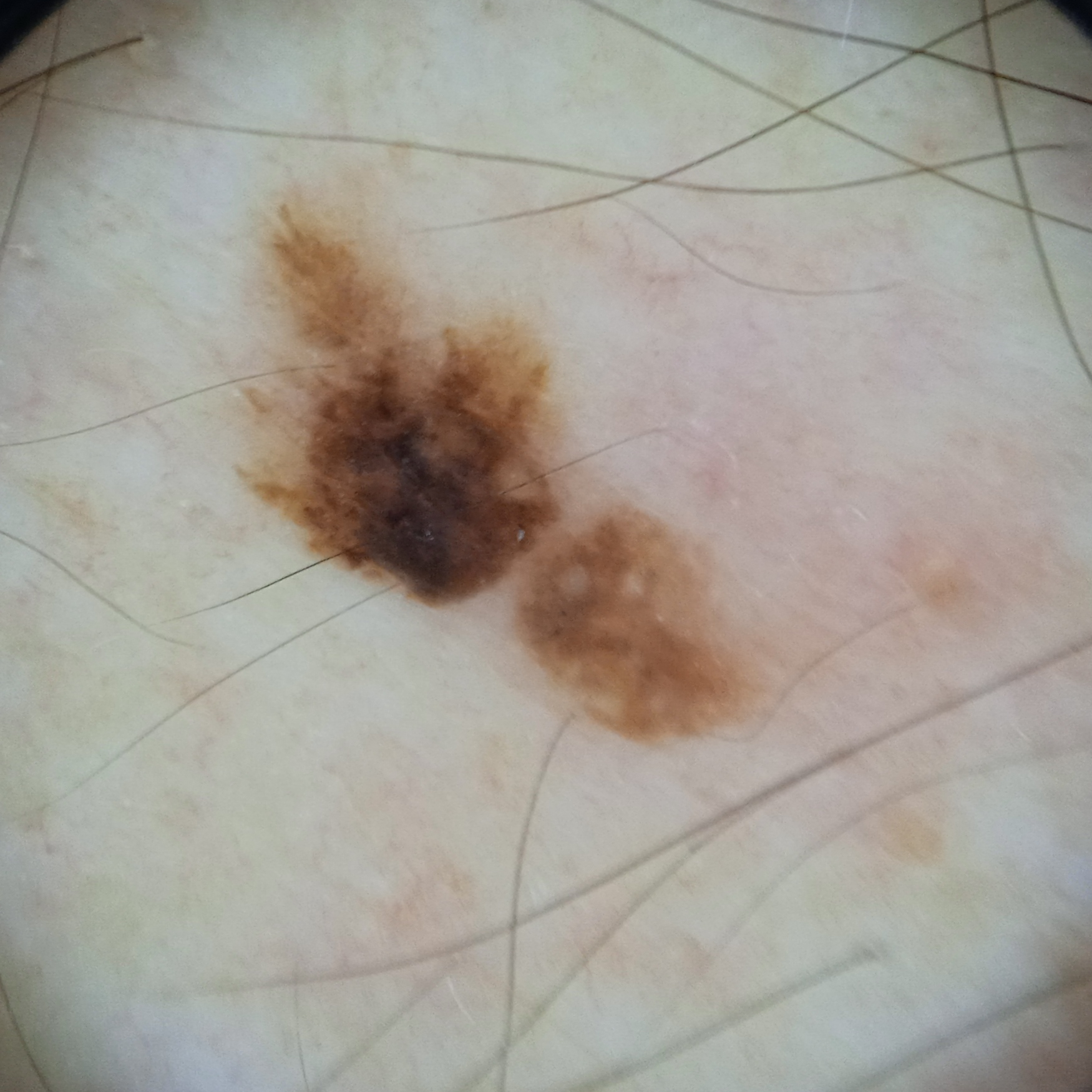{
  "image": "dermoscopy",
  "referral": "research study (no referral diagnosis)",
  "patient": {
    "age": 76,
    "sex": "male"
  },
  "sun_reaction": "skin reddens with sun exposure",
  "mole_burden": "few melanocytic nevi overall",
  "risk_factors": {
    "positive": [
      "a personal history of cancer",
      "a personal history of skin cancer"
    ],
    "negative": [
      "no family history of skin cancer"
    ]
  },
  "lesion_location": "the back",
  "lesion_size": {
    "diameter_mm": 7.8
  },
  "diagnosis": {
    "name": "seborrheic keratosis",
    "malignancy": "benign"
  }
}